The patient considered this hair loss; Fitzpatrick skin type IV; no constitutional symptoms were reported; this is a close-up image; located on the leg; texture is reported as raised or bumpy and rough or flaky — 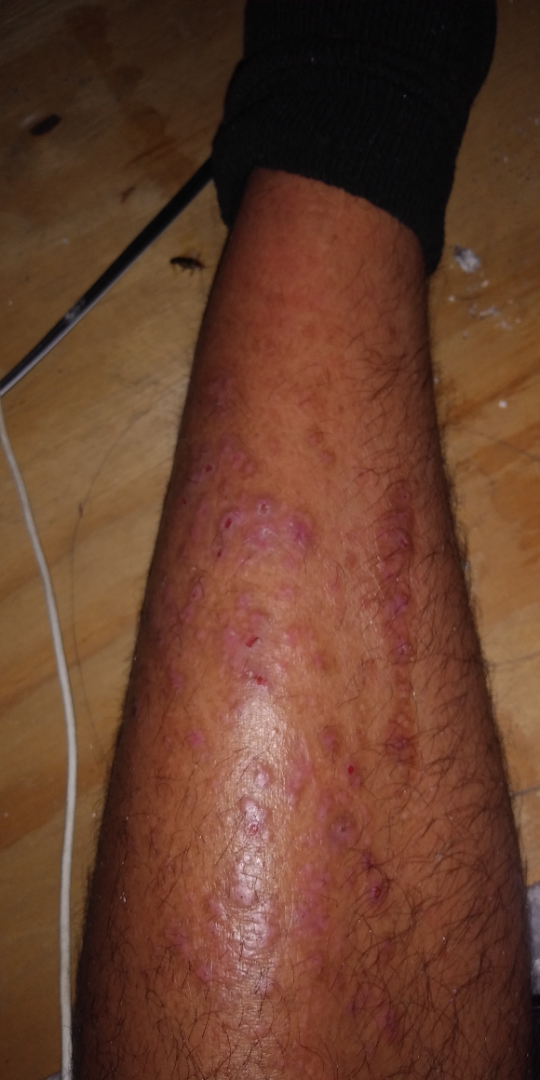On dermatologist assessment of the image: the differential is split between Lichen planus/lichenoid eruption and Prurigo nodularis; a more distant consideration is Drug Rash.